A female subject aged 68 to 72 · this is a dermoscopic photograph of a skin lesion.
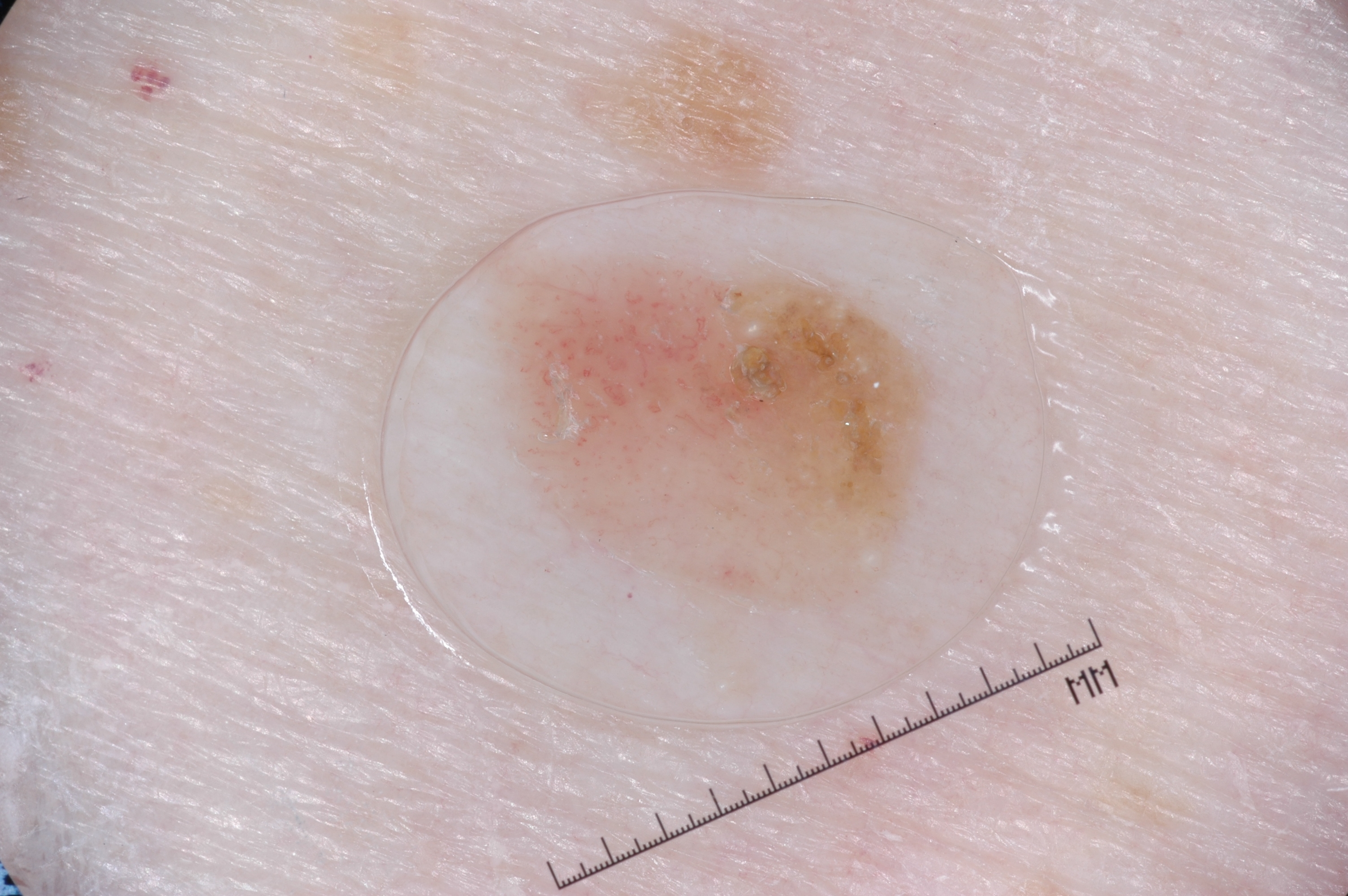lesion bbox=[479, 246, 935, 620]; dermoscopic pattern=milia-like cysts; assessment=a seborrheic keratosis, a benign lesion.